A dermoscopy image of a single skin lesion: 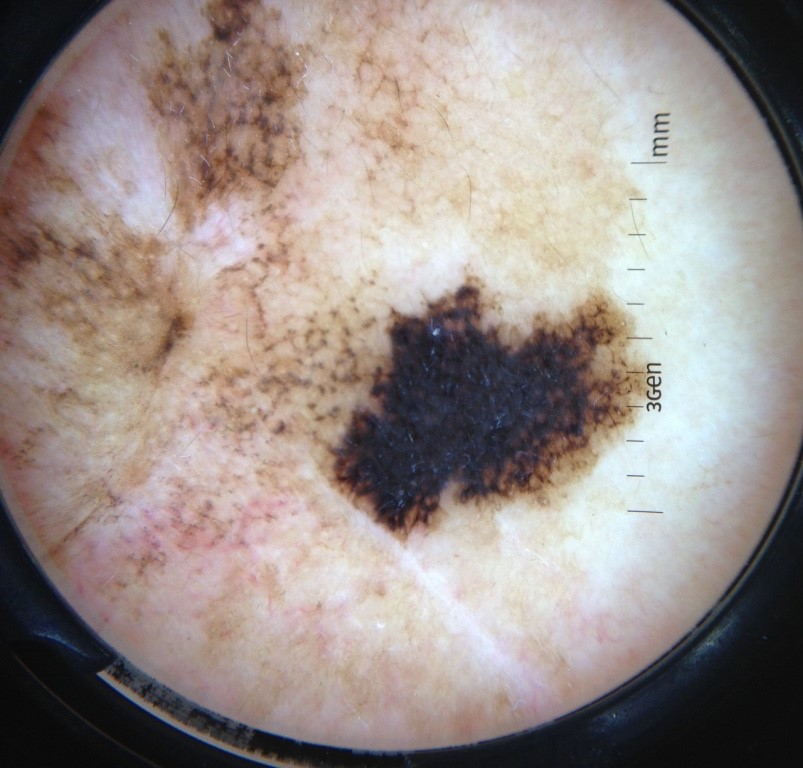Findings:
• diagnostic label — lentigo maligna (biopsy-proven)